This is a close-up image — 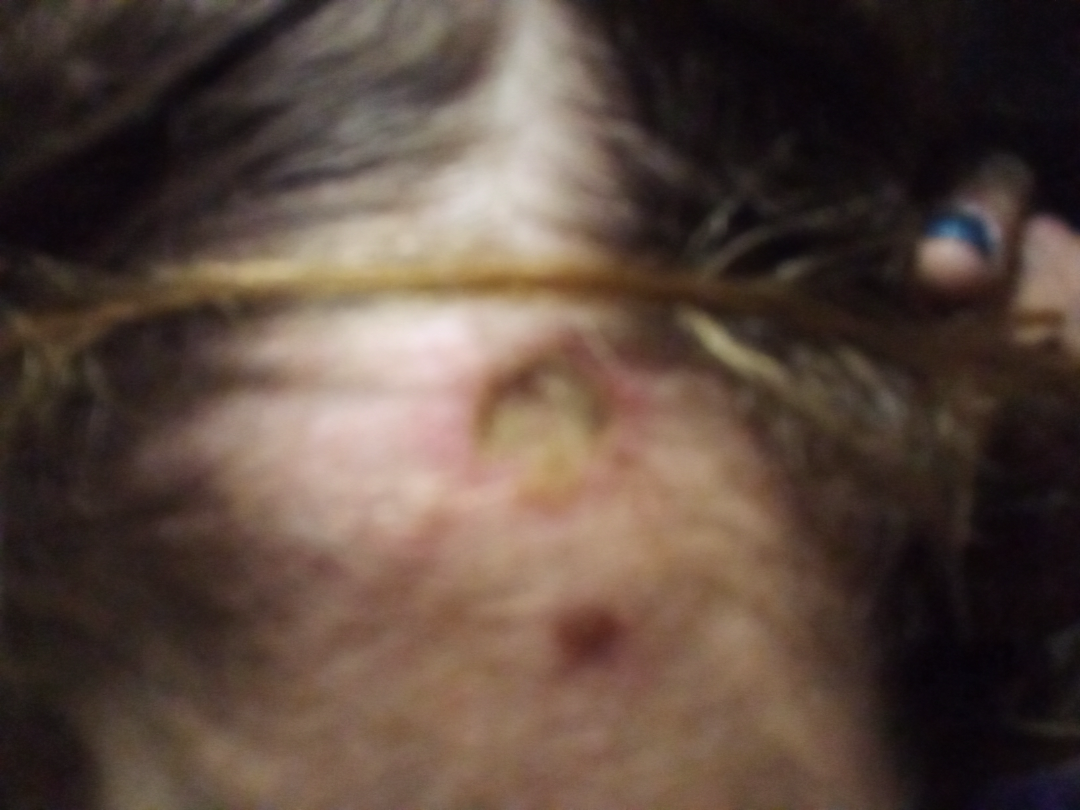assessment = could not be assessed